The back of the torso is involved. The condition has been present for one to three months. Non-clinician graders estimated a Monk skin tone scale of 2. The patient notes the lesion is flat, fluid-filled and raised or bumpy. This is a close-up image. Symptoms reported: bothersome appearance, burning, pain, darkening and itching. The contributor is 30–39, male. No constitutional symptoms were reported: 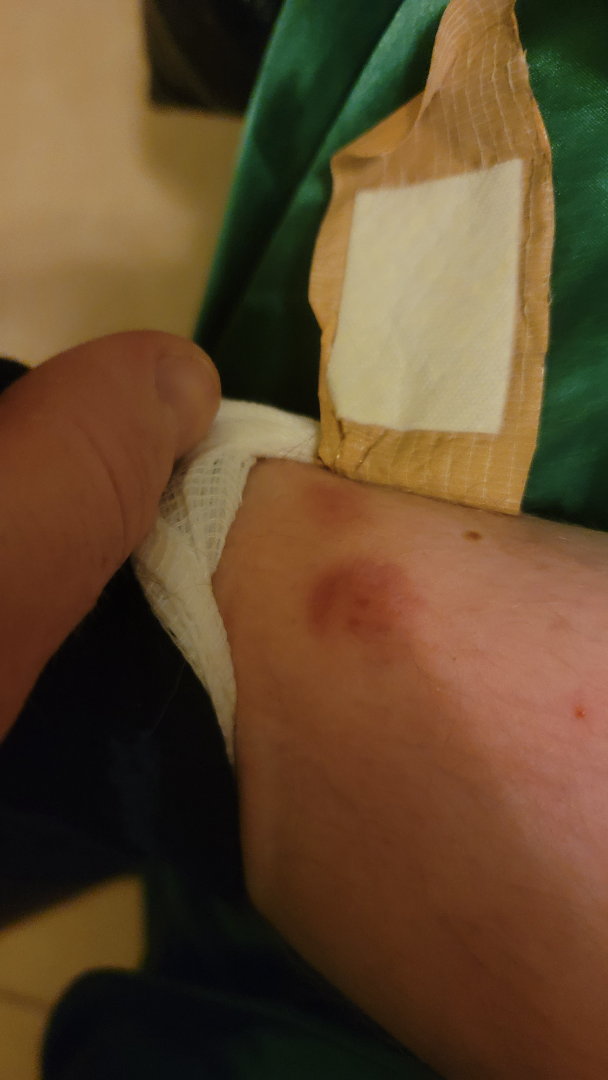Reviewed remotely by three dermatologists: the favored diagnosis is ecchymoses; the differential also includes Insect Bite; less likely is Pigmented purpuric eruption; a remote consideration is Allergic Contact Dermatitis.